A dermoscopic close-up of a skin lesion: 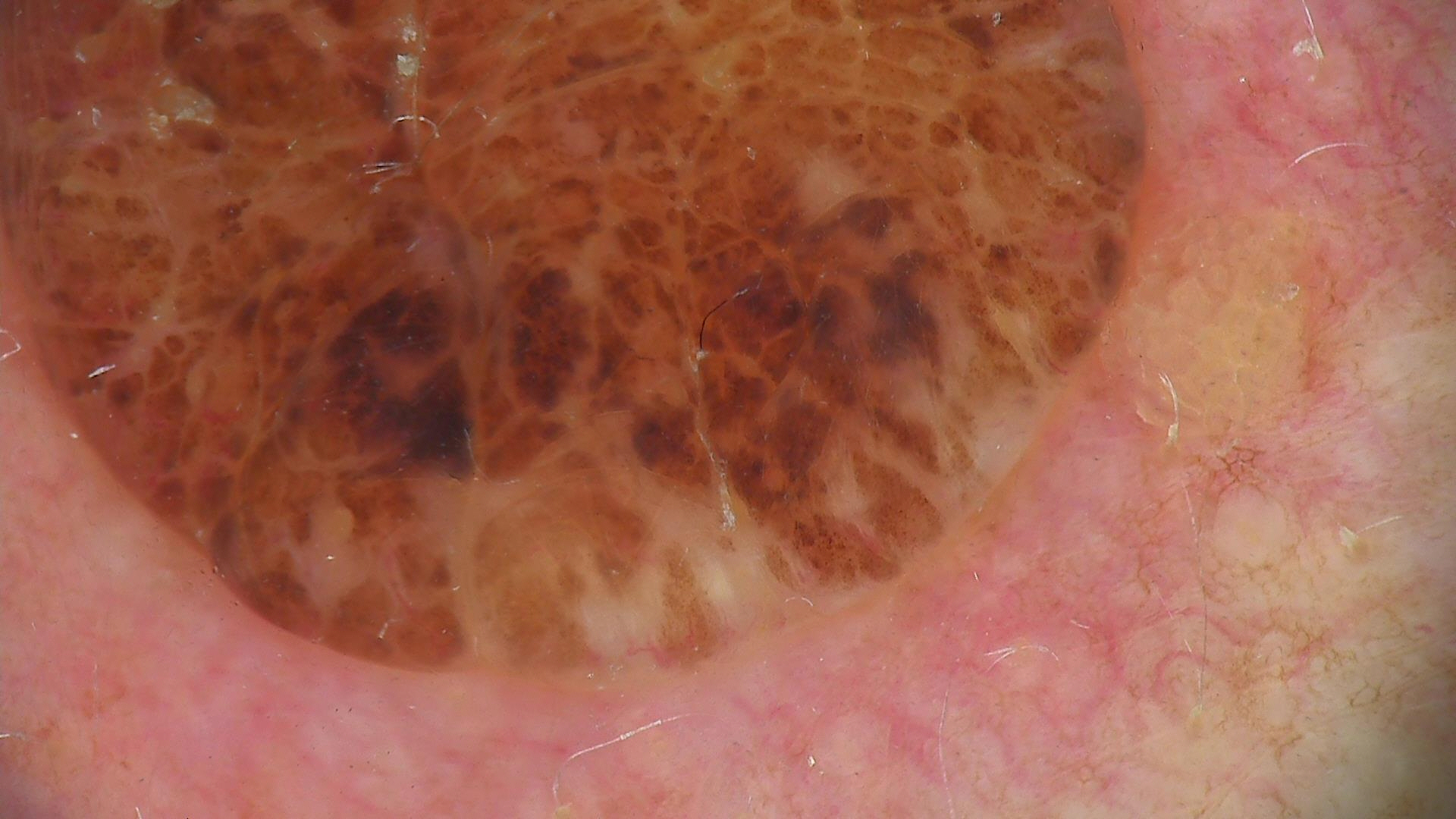  lesion_type:
    main_class: banal
    pattern: dermal
  diagnosis:
    name: dermal nevus
    code: db
    malignancy: benign
    super_class: melanocytic
    confirmation: expert consensus